An image taken at a distance. The subject is female. The affected area is the top or side of the foot:
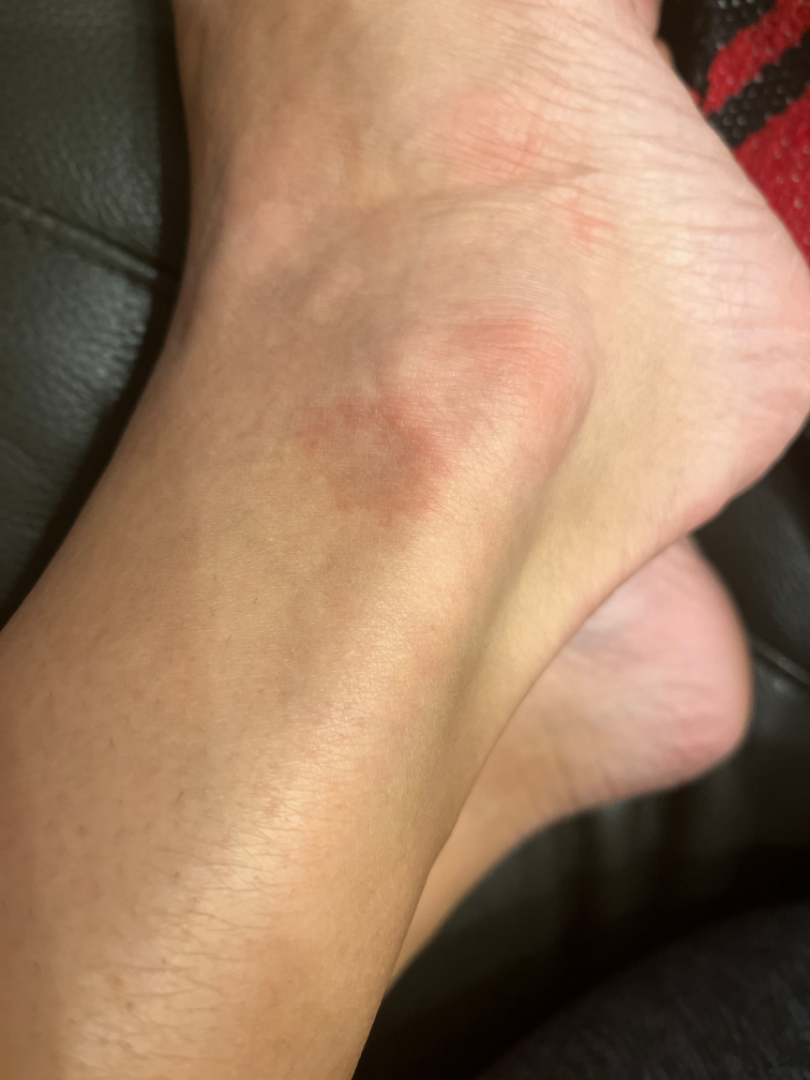History:
Symptoms reported: enlargement, bothersome appearance and darkening. The patient considered this skin that appeared healthy to them. Skin tone: lay graders estimated MST 2 or 3.
Impression:
On remote review of the image: the leading impression is Eczema; with consideration of Pigmented purpuric eruption.